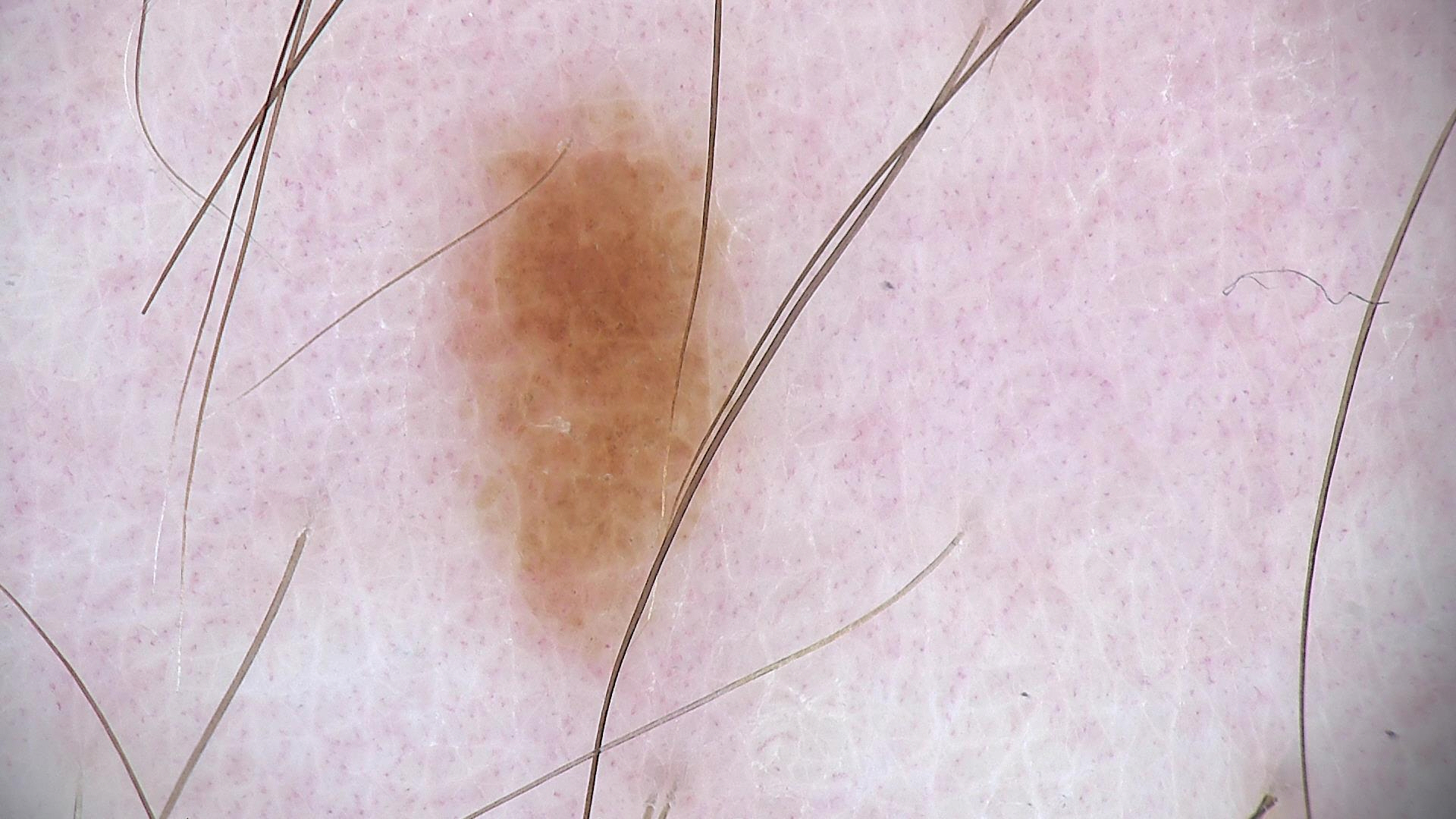Q: What is the imaging modality?
A: dermatoscopy
Q: What is the diagnosis?
A: dysplastic junctional nevus (expert consensus)